The photograph was taken at an angle; female subject, age 50–59:
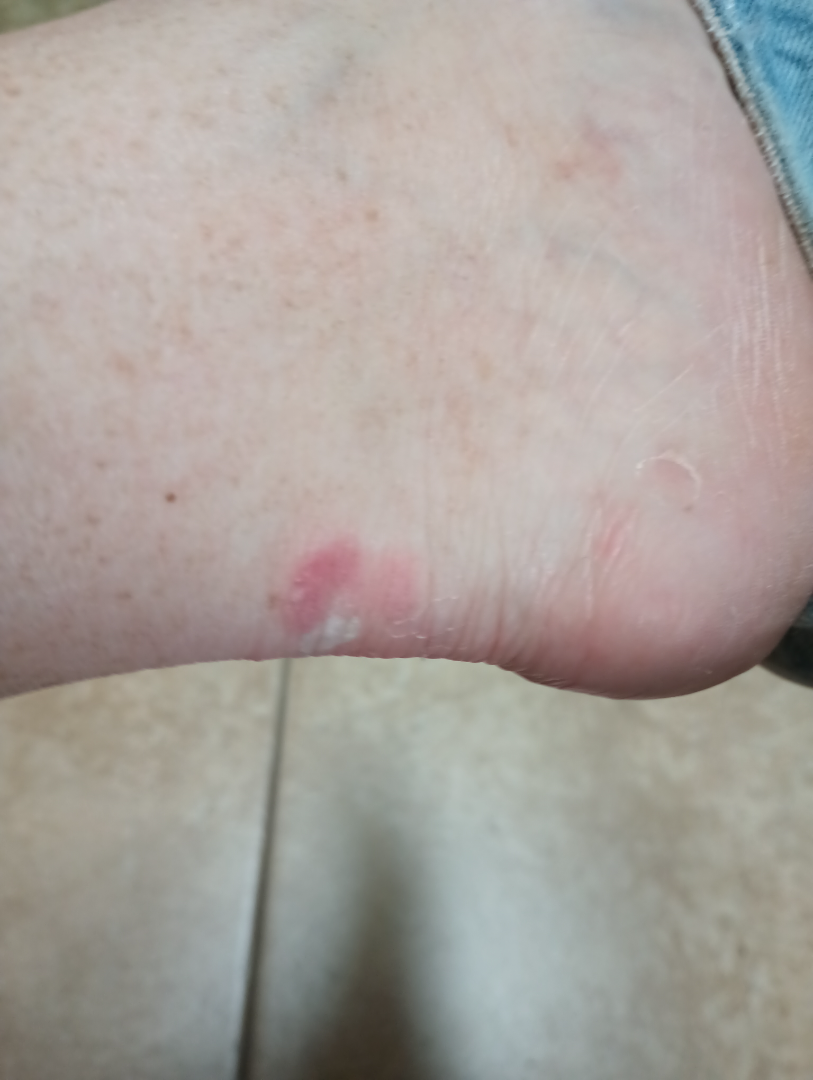assessment — not assessable